A dermatoscopic image of a skin lesion.
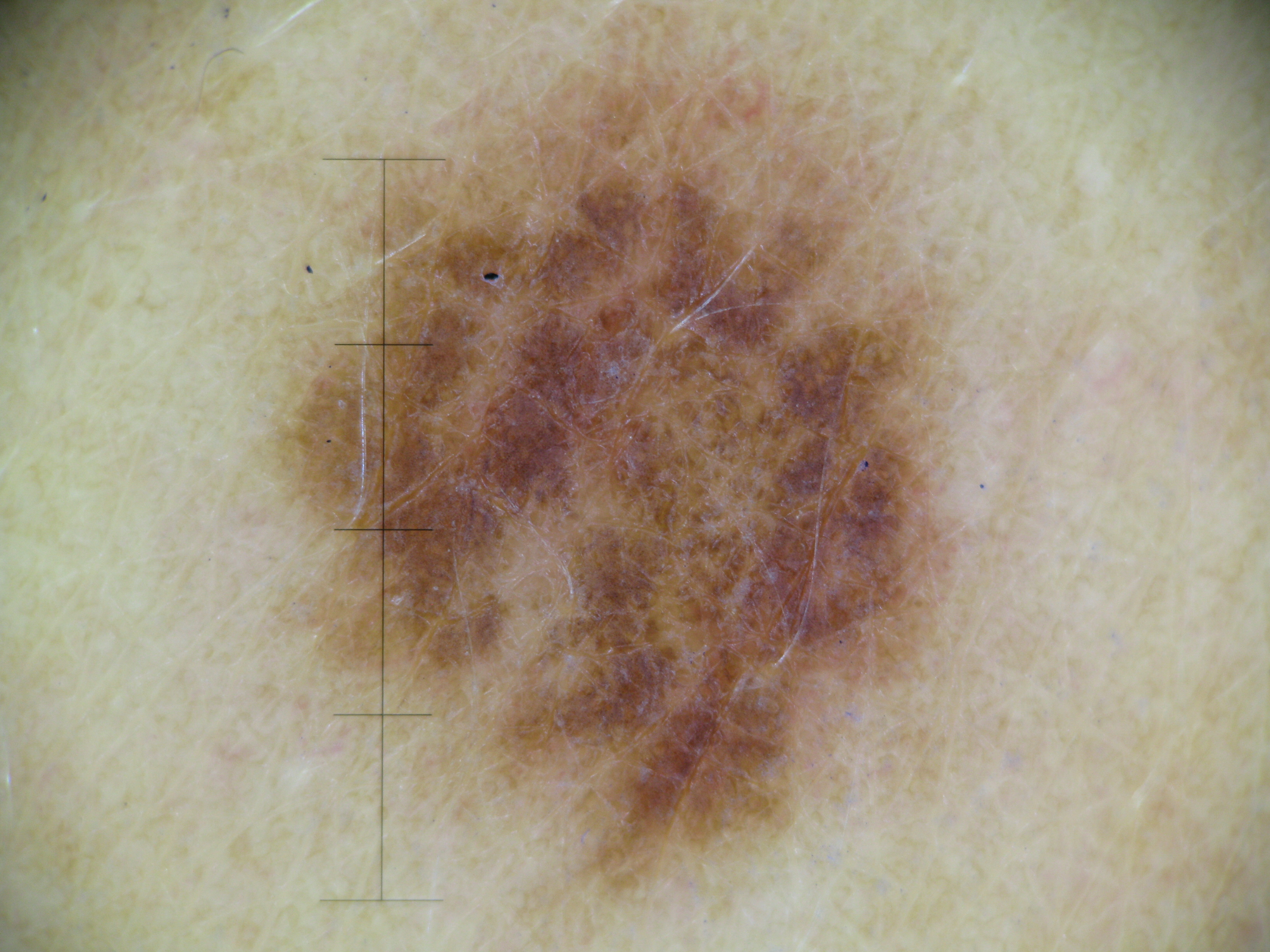Consistent with a dysplastic compound nevus.